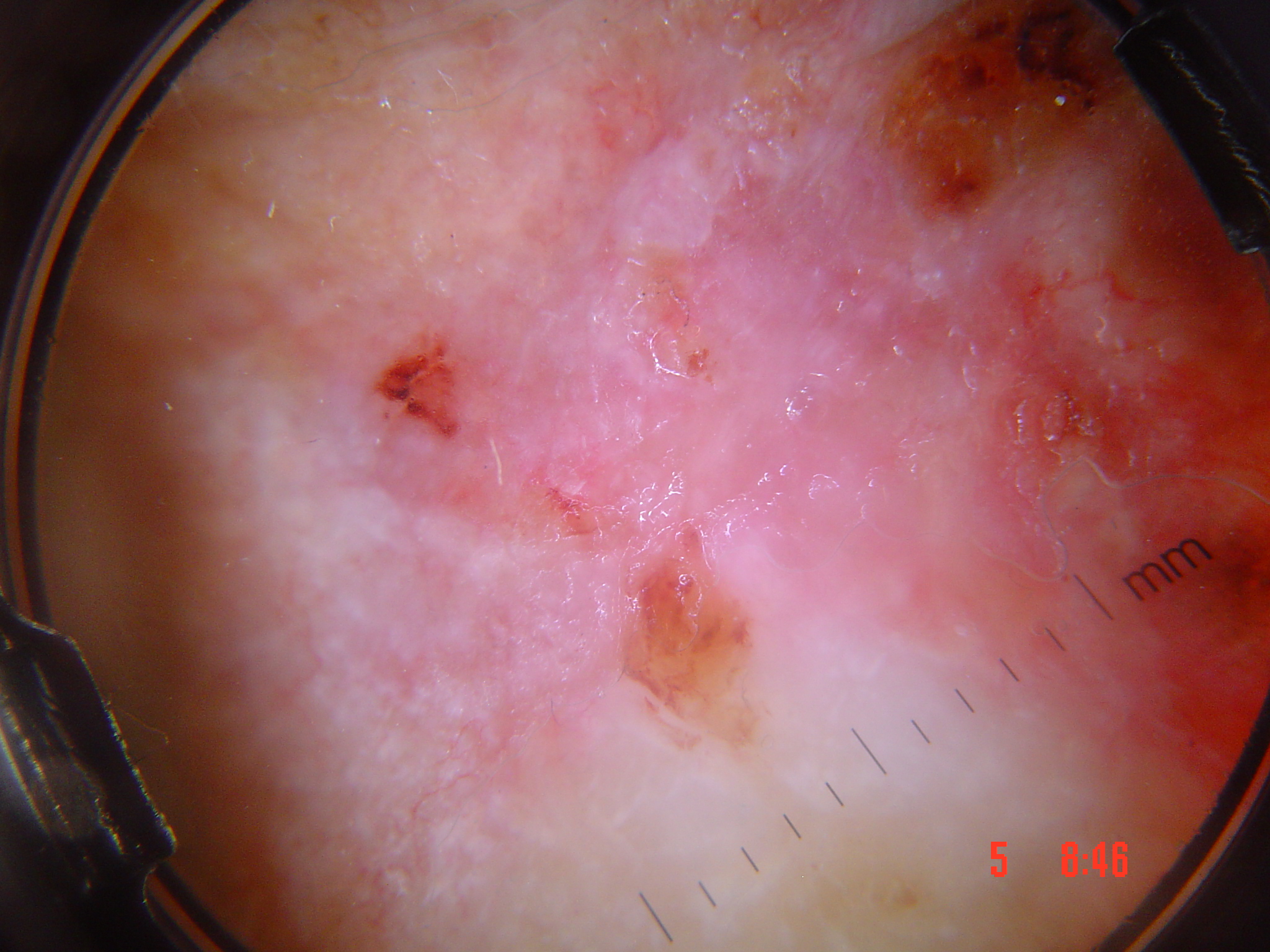  image: dermatoscopy
  lesion_type:
    main_class: keratinocytic
  diagnosis:
    name: squamous cell carcinoma
    code: scc
    malignancy: malignant
    super_class: non-melanocytic
    confirmation: histopathology